The photograph was taken at a distance. The patient is 18–29, female. Located on the head or neck, front of the torso and back of the torso.
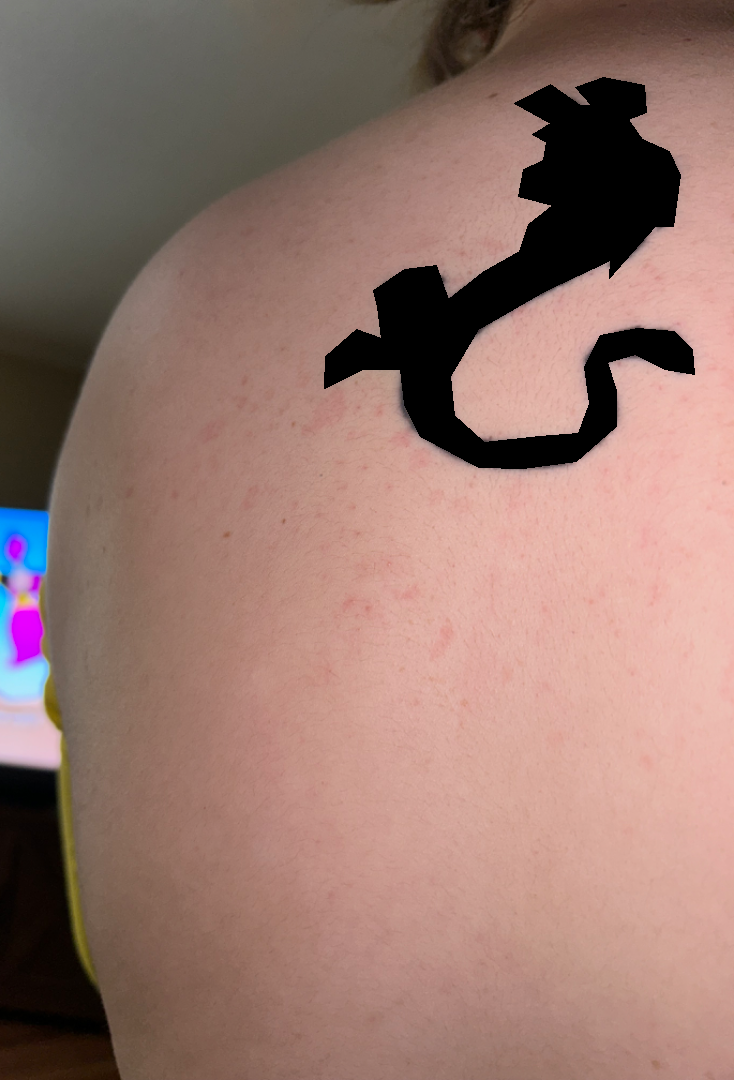<dermatology_case>
<skin_tone>
  <fitzpatrick>II</fitzpatrick>
  <monk_skin_tone>2</monk_skin_tone>
</skin_tone>
<symptoms>bothersome appearance, enlargement, darkening</symptoms>
<patient_category>a rash</patient_category>
<differential>
  <Contact dermatitis>0.35</Contact dermatitis>
  <Tinea Versicolor>0.35</Tinea Versicolor>
  <Pityriasis rosea>0.18</Pityriasis rosea>
  <Drug Rash>0.12</Drug Rash>
</differential>
</dermatology_case>